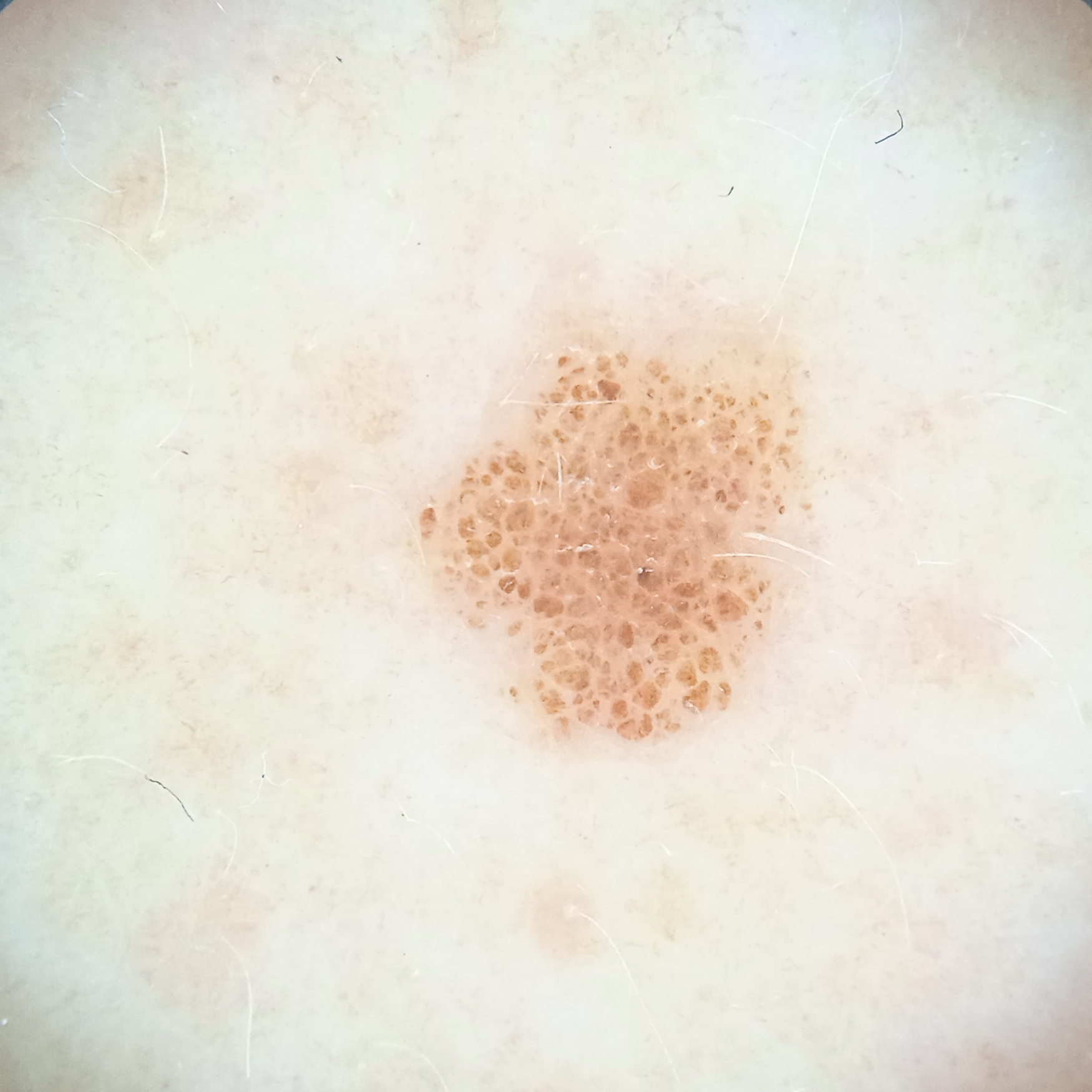<case>
<risk_factors>
<positive>a personal history of skin cancer</positive>
</risk_factors>
<image>dermatoscopic image</image>
<sun_reaction>skin reddens with sun exposure</sun_reaction>
<lesion_location>the back</lesion_location>
<lesion_size>
<diameter_mm>5.1</diameter_mm>
</lesion_size>
<diagnosis>
<name>melanocytic nevus</name>
<malignancy>benign</malignancy>
</diagnosis>
</case>